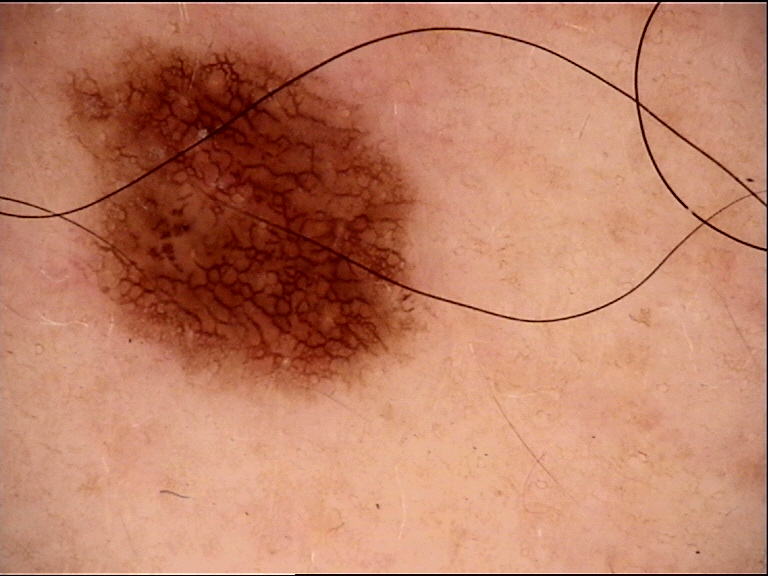class — dysplastic junctional nevus (expert consensus)